A dermatoscopic image of a skin lesion.
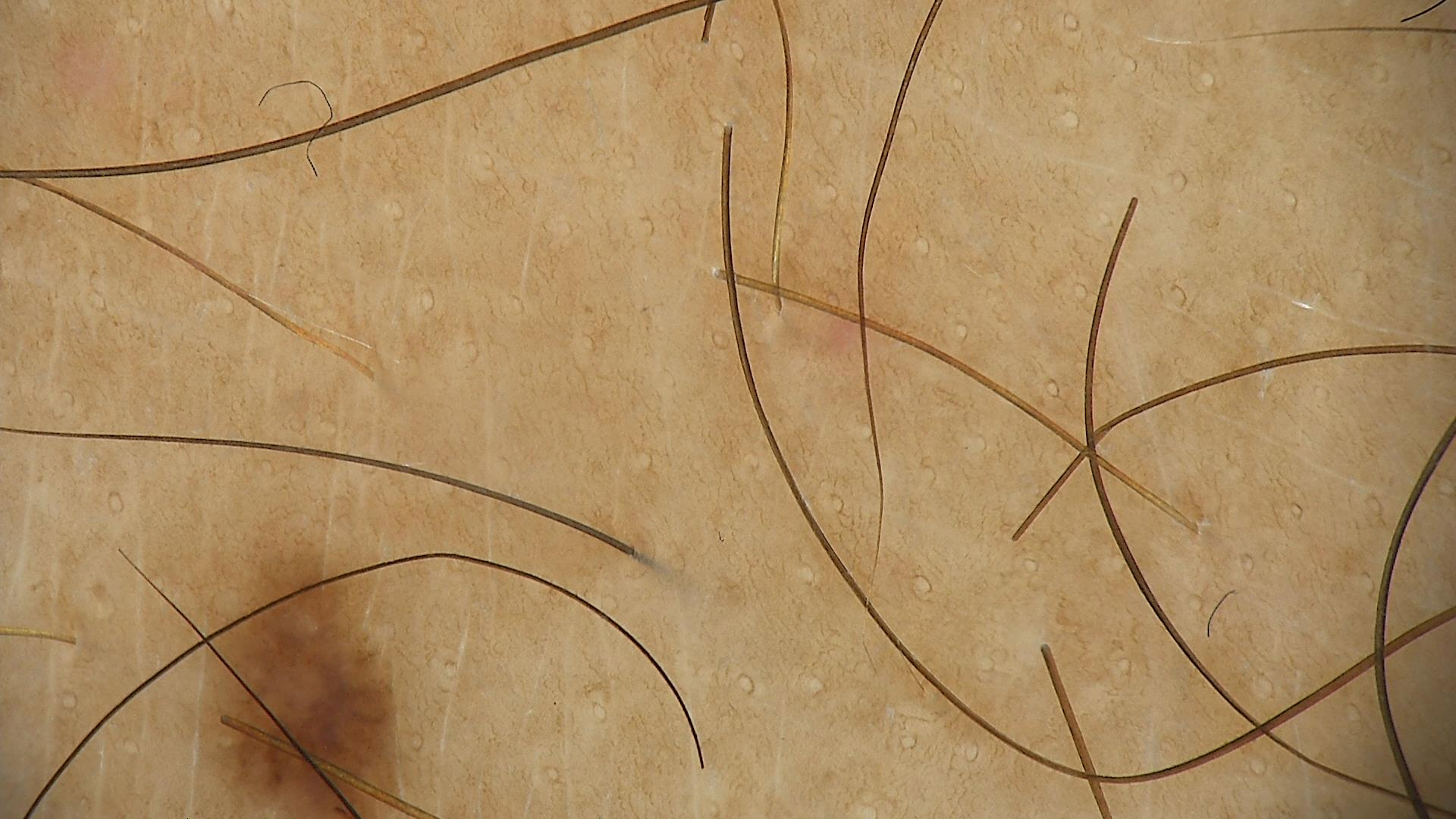This is a banal lesion.
Classified as a junctional nevus.